A dermatoscopic image of a skin lesion — 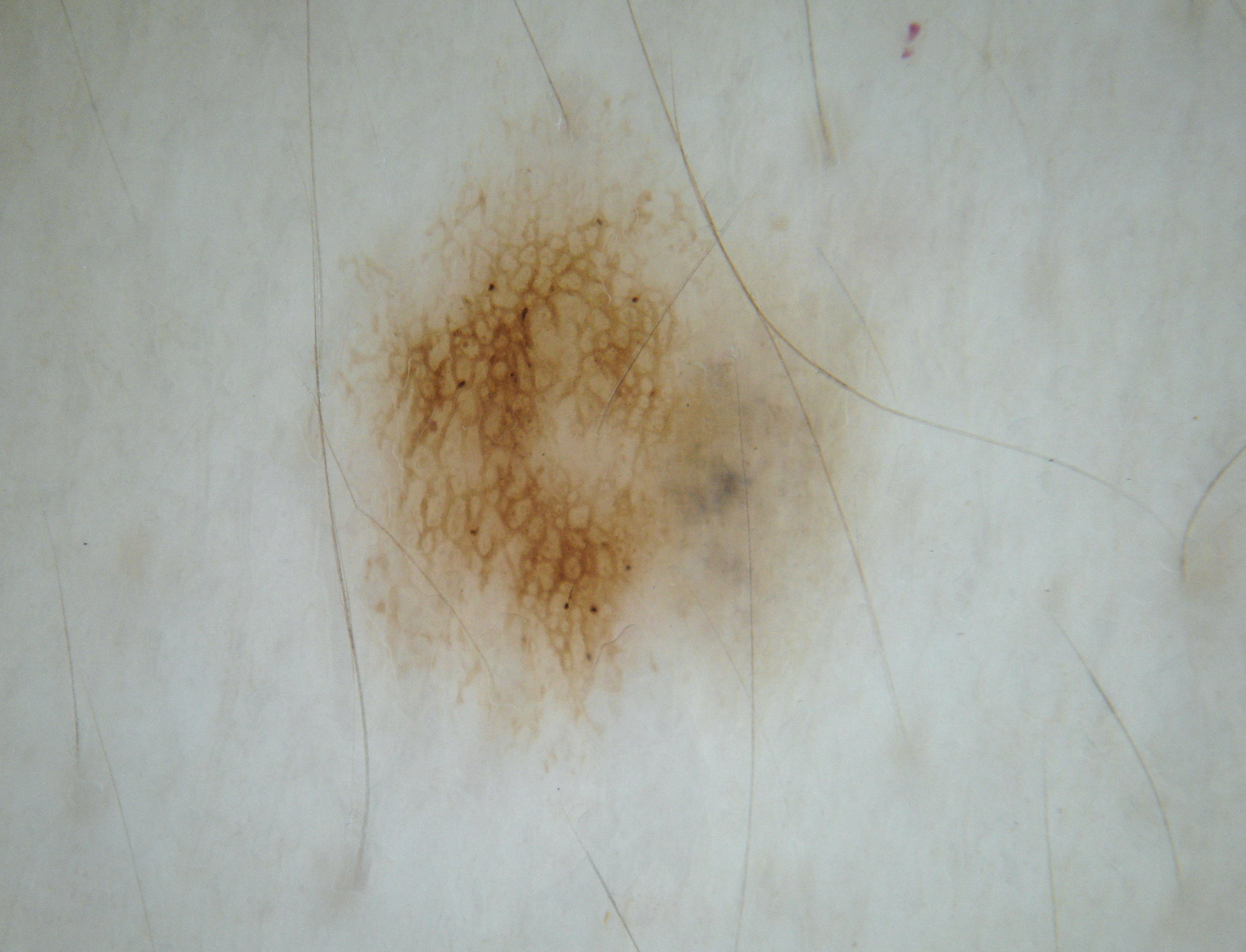As (left, top, right, bottom), the lesion occupies the region 307/60/878/770. The diagnostic assessment was a melanocytic nevus.